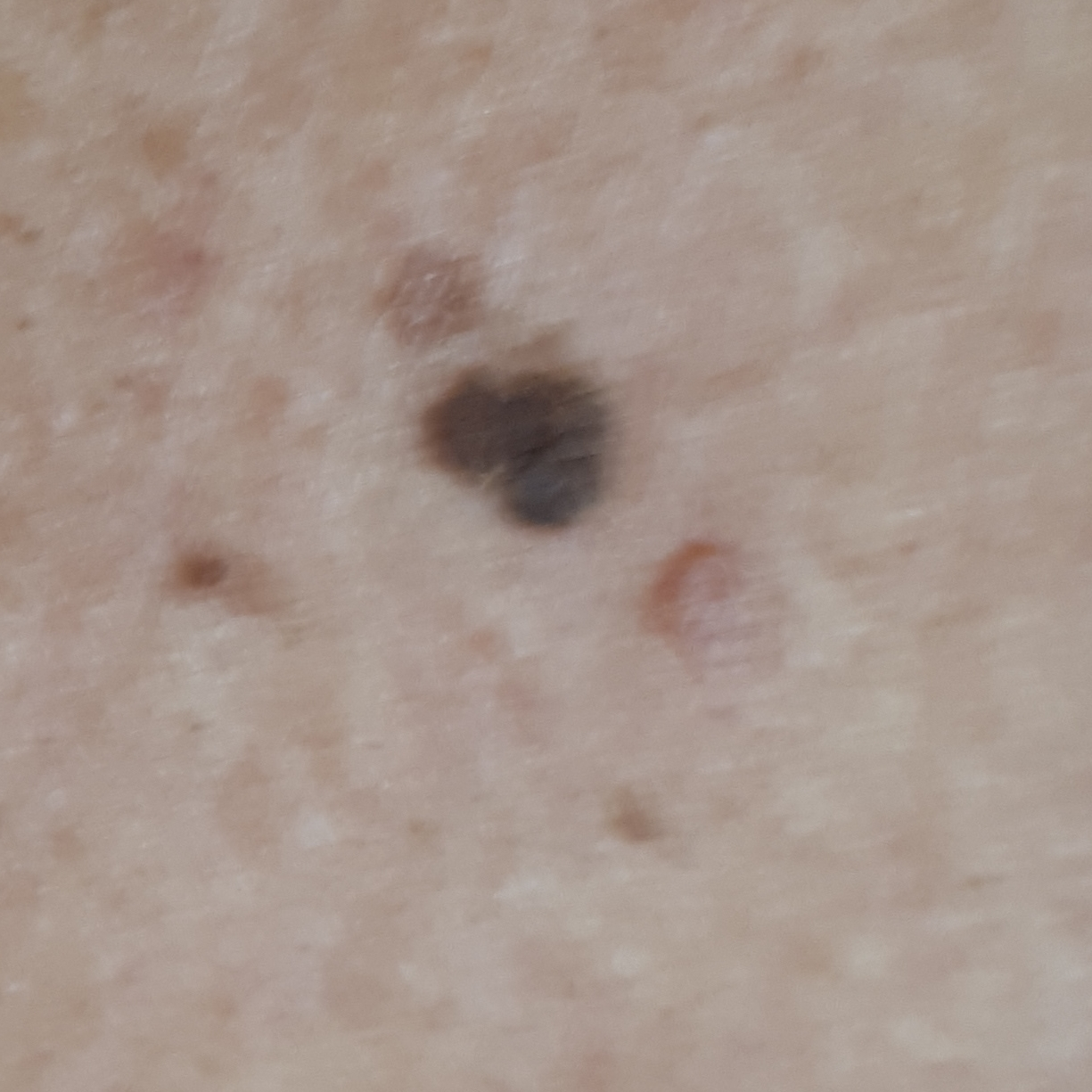Summary: A clinical photograph of a skin lesion. Located on the chest. Per patient report, the lesion has grown and is elevated. Conclusion: The consensus clinical diagnosis was a seborrheic keratosis.